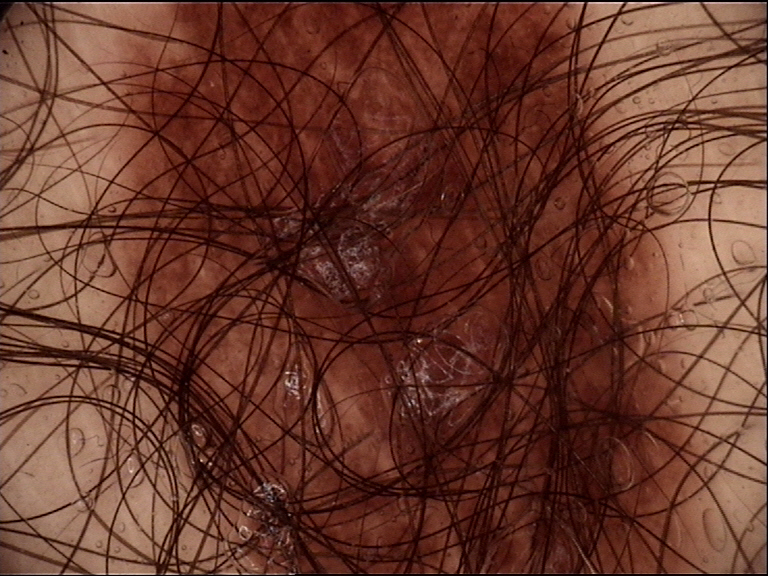A dermatoscopic image of a skin lesion. Classified as a dysplastic junctional nevus.